The photo was captured at an angle — 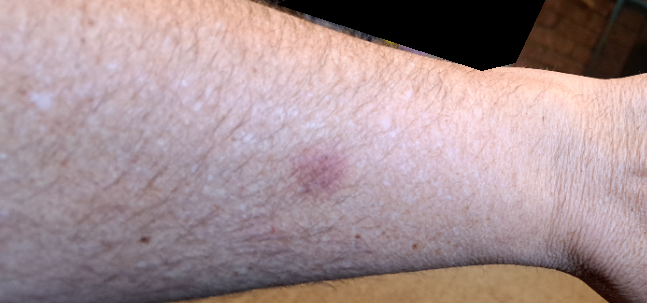assessment: not assessable.